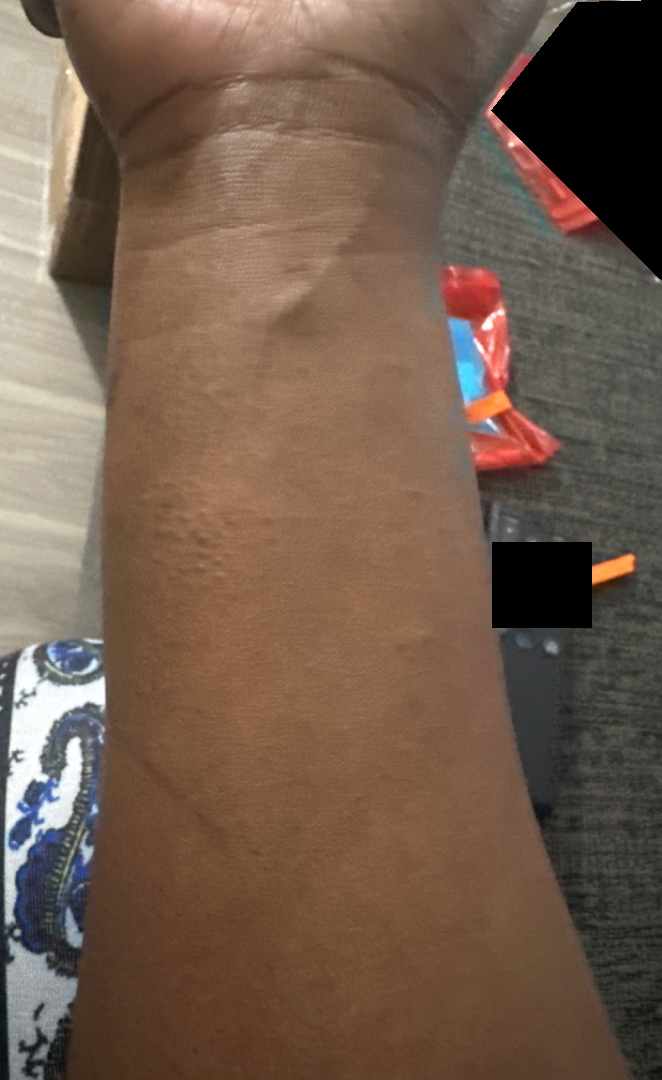Assessment: The reviewer was unable to grade this case for skin condition. Clinical context: The lesion involves the arm. Close-up view.